A dermoscopic image of a skin lesion: 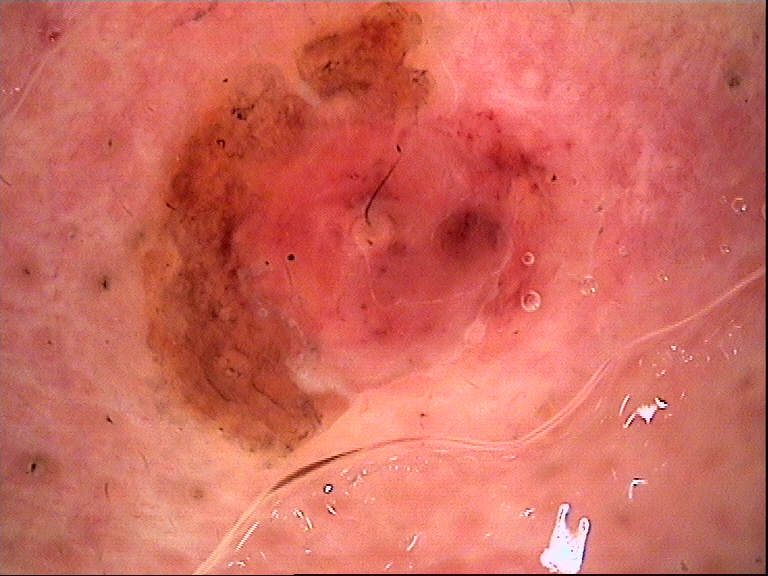Histopathology confirmed a malignant, keratinocytic lesion — a squamous cell carcinoma.